Texture is reported as flat. The patient notes the condition has been present for less than one week. The lesion involves the leg. The lesion is associated with darkening, enlargement, bothersome appearance and burning. The photograph was taken at an angle.
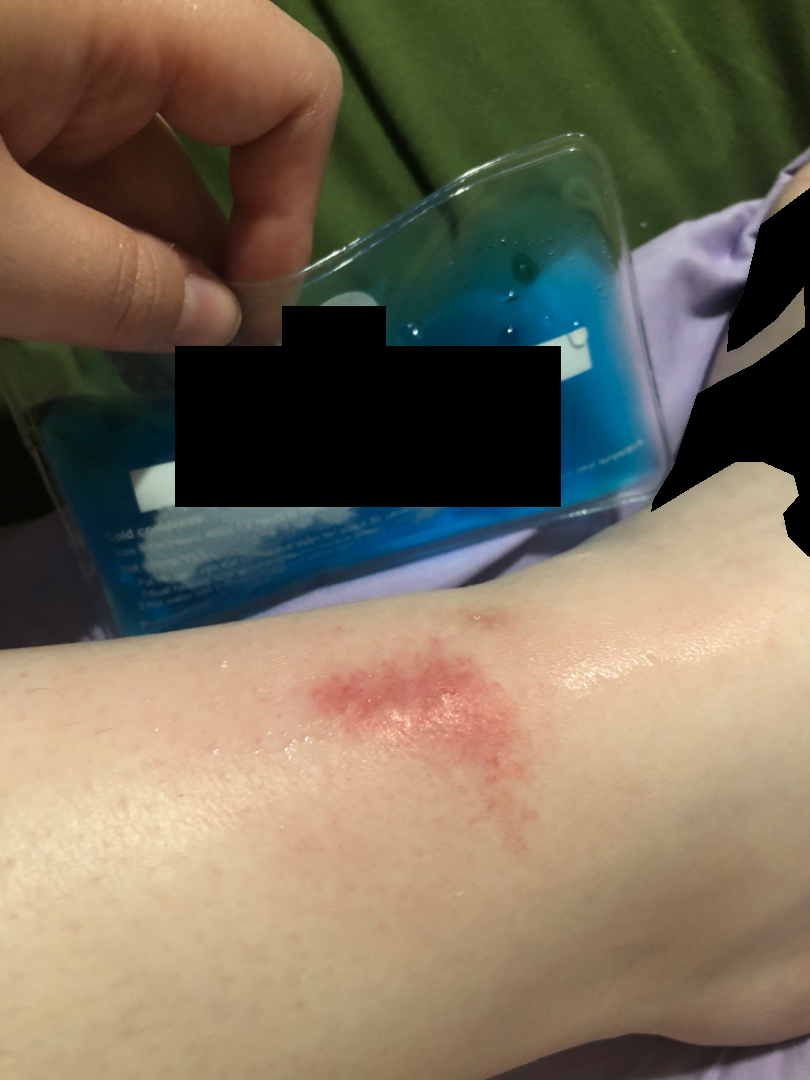Q: What is the dermatologist's impression?
A: Pigmented purpuric eruption (weight 0.50); Eczema (weight 0.50)